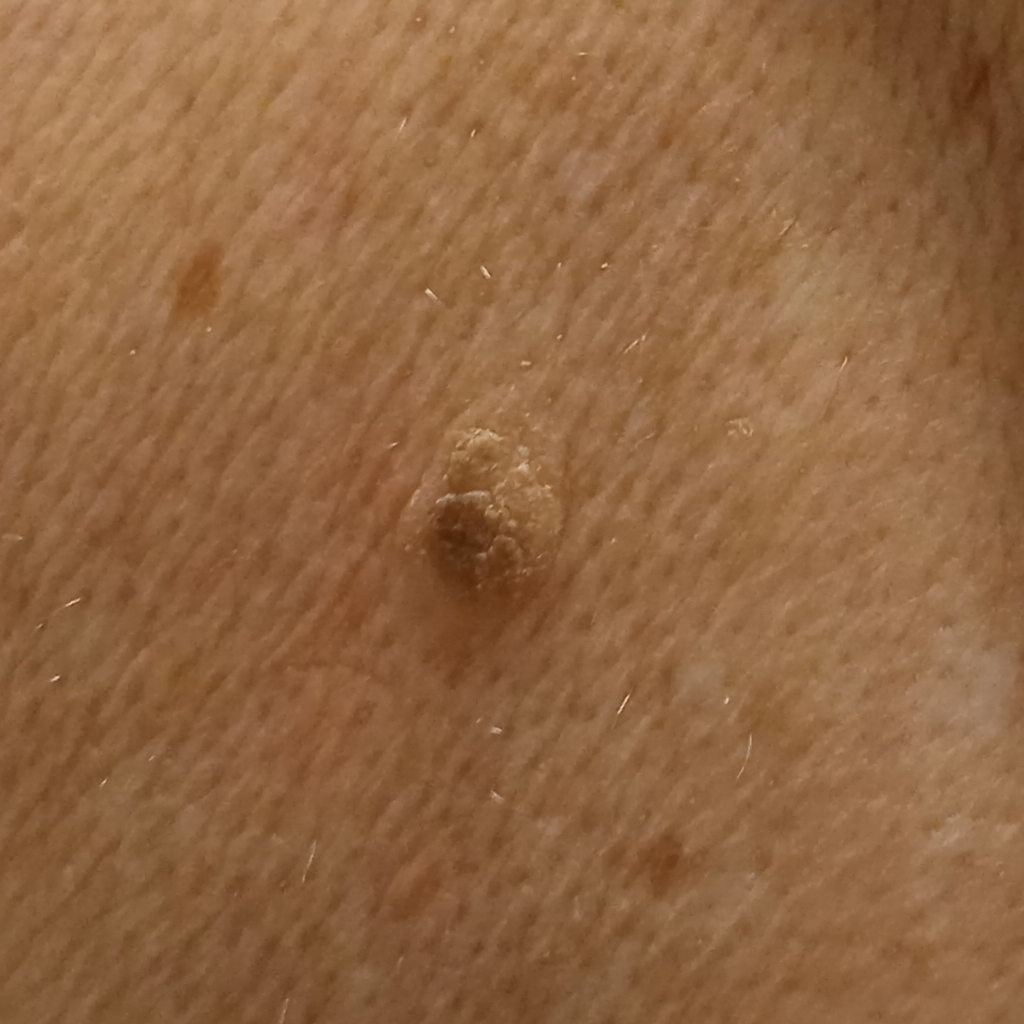Collected as part of a research study, without a referral diagnosis. A clinical photograph showing a skin lesion. A female subject 73 years of age. The patient says their skin reddens with sun exposure. The lesion measures approximately 8.6 mm. The diagnostic impression was a seborrheic keratosis.